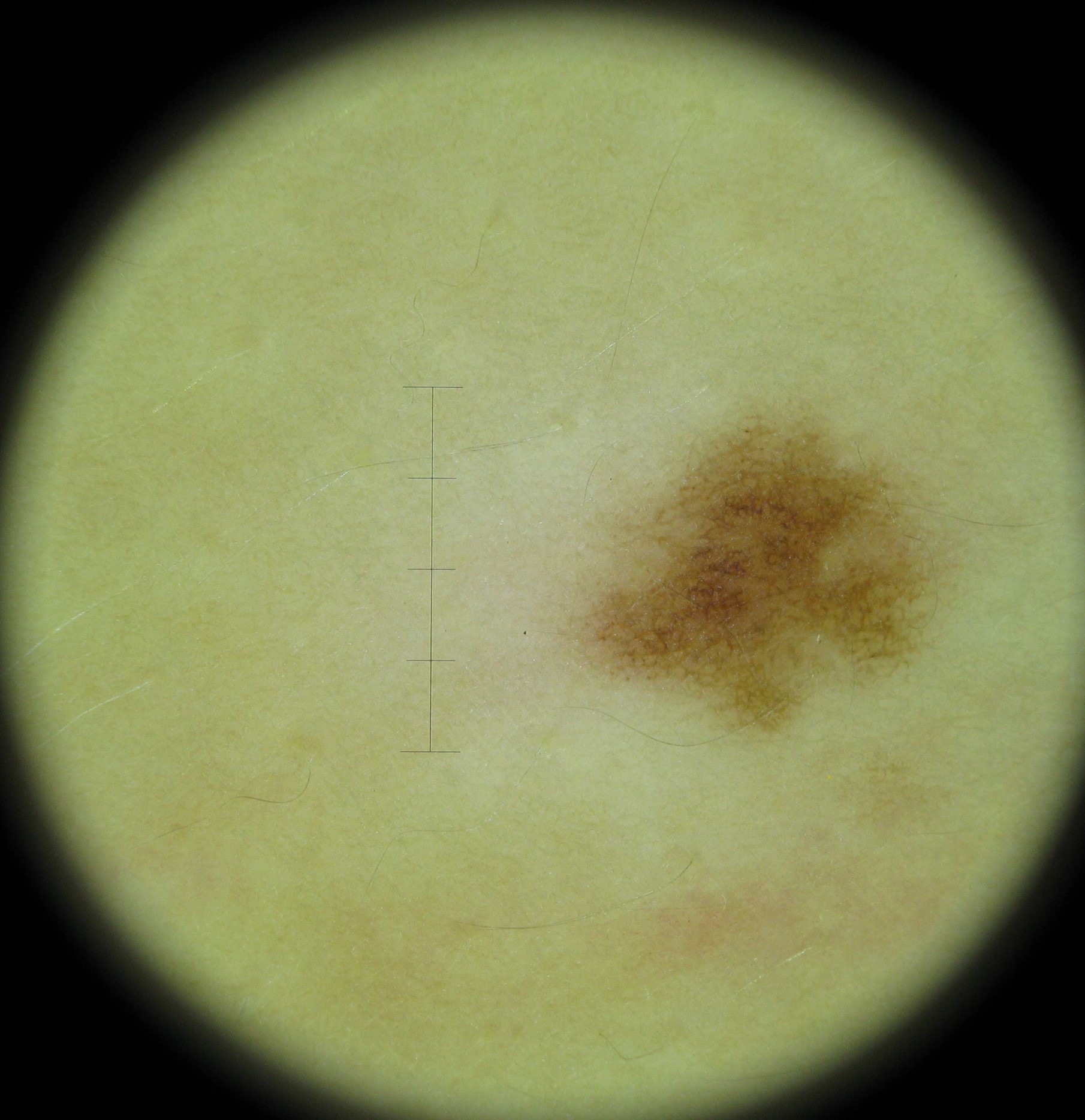modality = dermatoscopy, diagnosis = dysplastic junctional nevus (expert consensus).